The affected area is the arm and back of the hand · the photograph is a close-up of the affected area · reported lesion symptoms include itching · the patient considered this a rash · male patient, age 50–59 · present for less than one week:
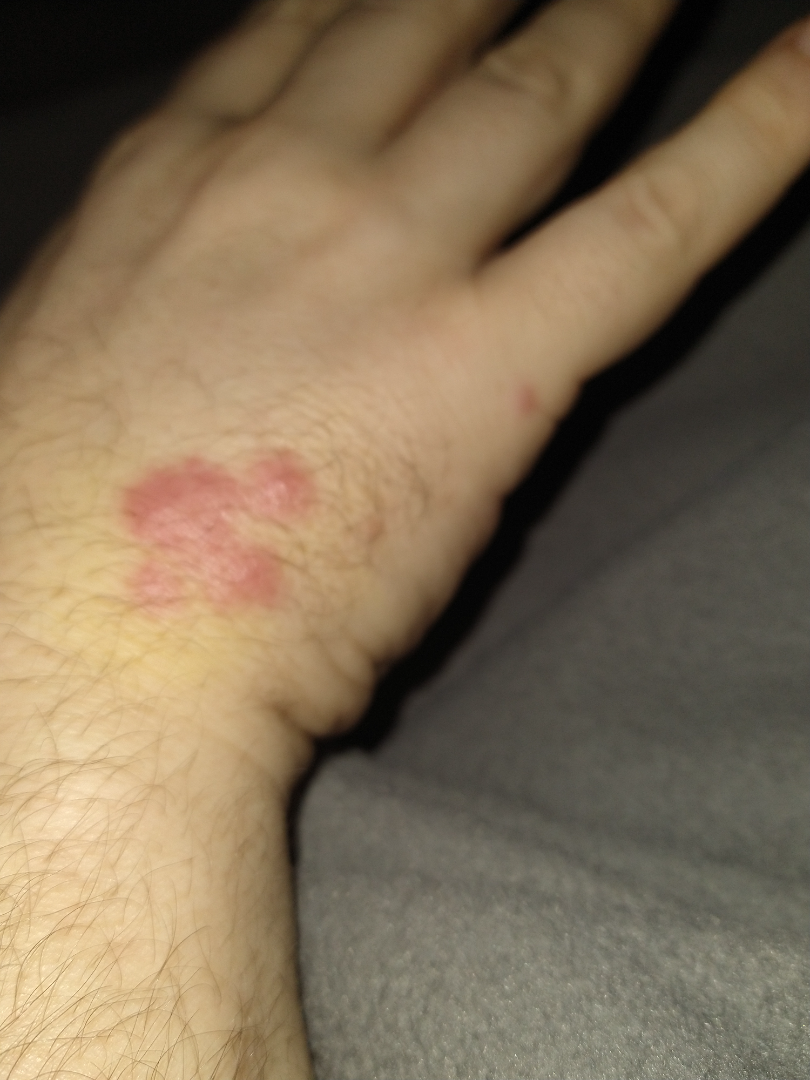| feature | finding |
|---|---|
| differential | Cutaneous sarcoidosis (possible); Skin and soft tissue atypical mycobacterial infection (possible); Granuloma annulare (possible); Insect Bite (unlikely); B-Cell Cutaneous Lymphoma (unlikely) |